A dermatoscopic image of a skin lesion — 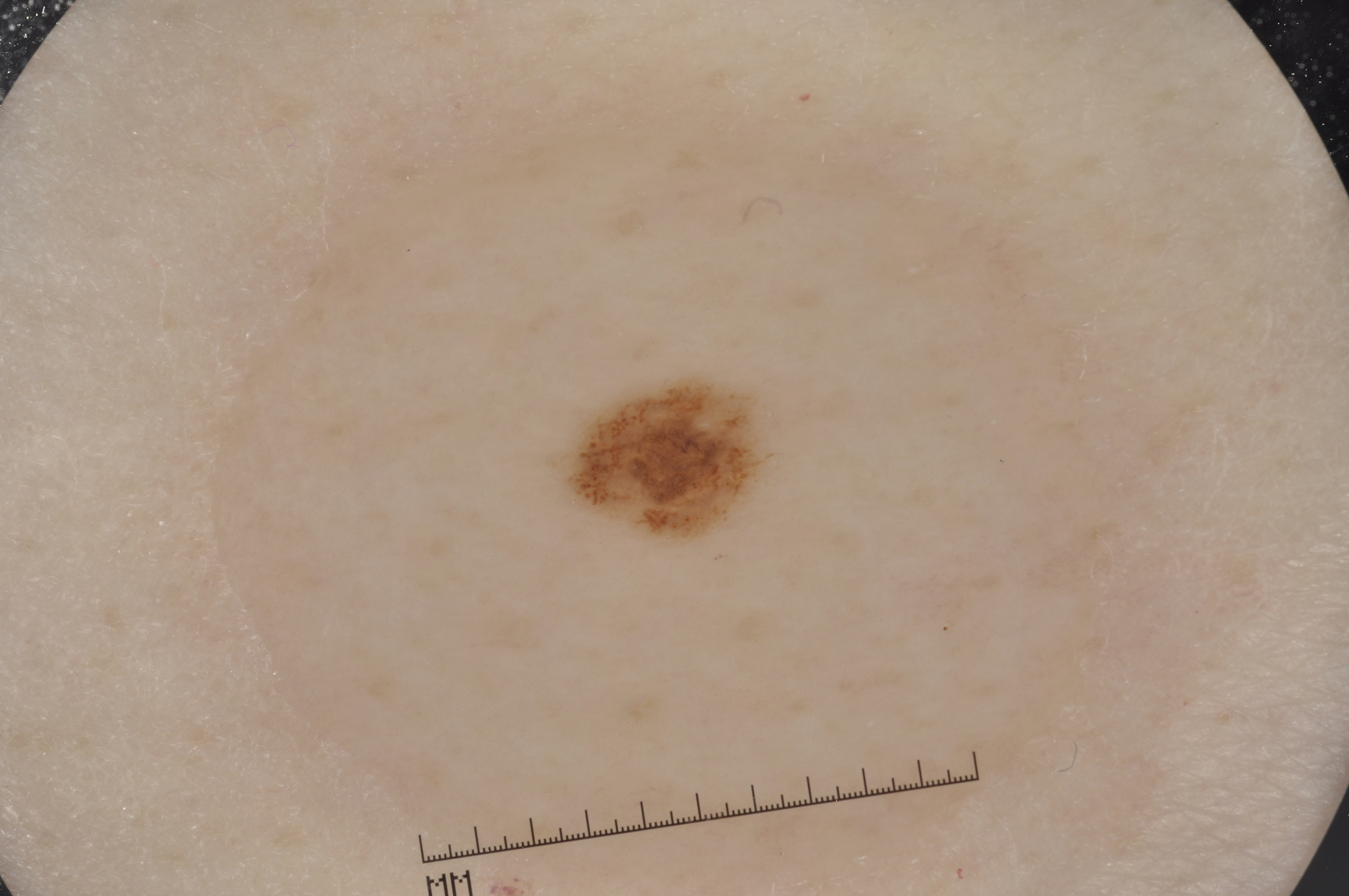With coordinates (x1, y1, x2, y2), lesion location: <bbox>545, 371, 775, 548</bbox>. Diagnosed as a melanocytic nevus, a benign lesion.